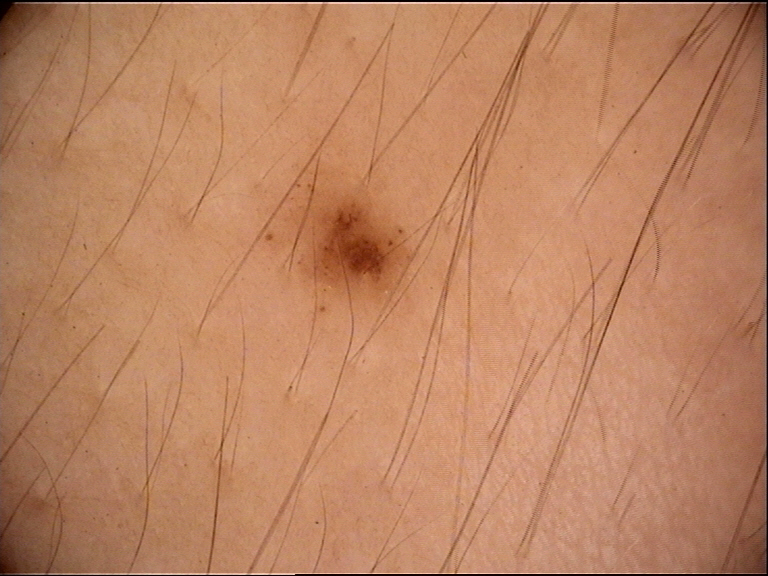image: dermoscopy
lesion_type:
  main_class: banal
  pattern: junctional
diagnosis:
  name: junctional nevus
  code: jb
  malignancy: benign
  super_class: melanocytic
  confirmation: expert consensus